A clinical photograph of a skin lesion · a subject 54 years old: 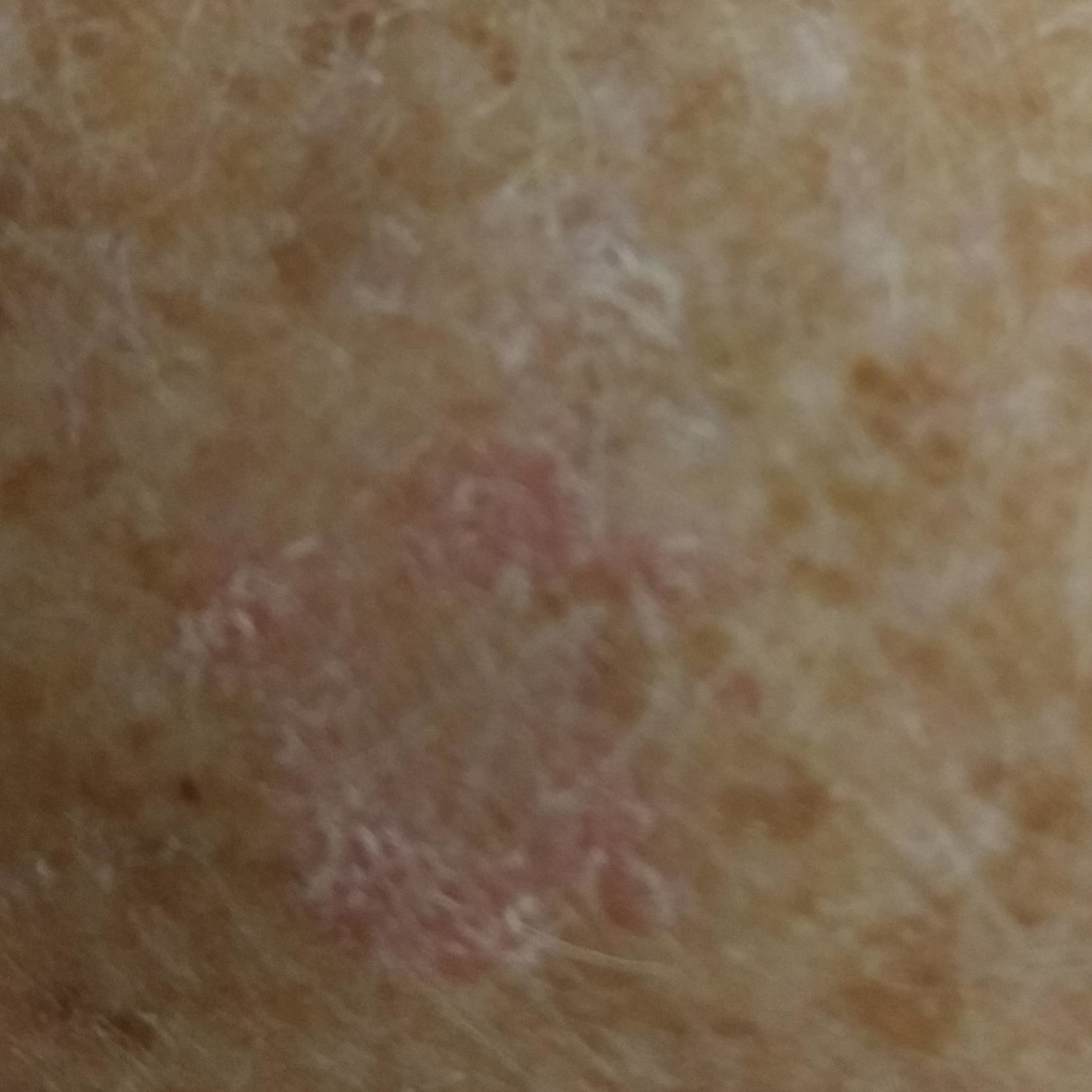Case summary:
The lesion involves a forearm. By the patient's account, the lesion itches.
Conclusion:
Clinically diagnosed as a lesion with uncertain malignant potential — an actinic keratosis.